A clinical photo of a skin lesion taken with a smartphone · a patient in their late 60s: 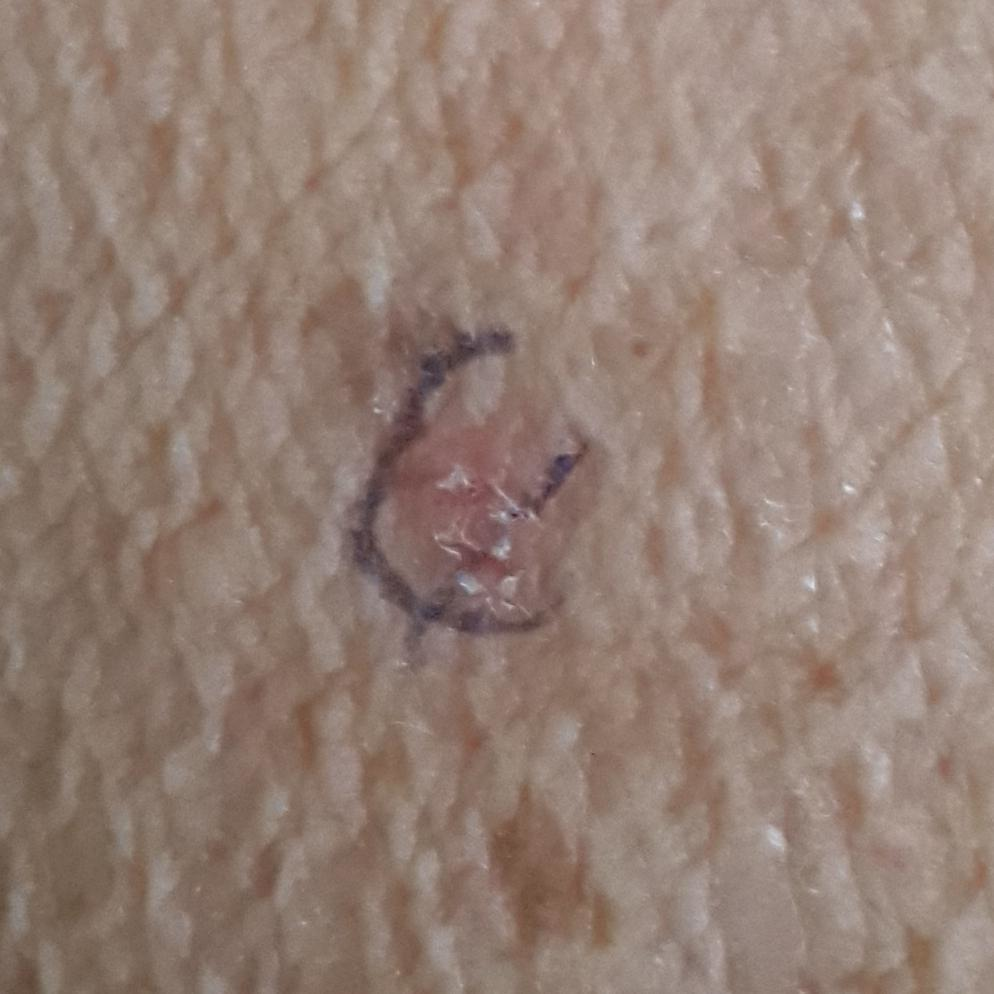{"lesion_location": "an arm", "symptoms": {"present": ["itching"]}, "diagnosis": {"name": "actinic keratosis", "code": "ACK", "malignancy": "indeterminate", "confirmation": "clinical consensus"}}